The lesion involves the leg · self-categorized by the patient as a rash · the lesion is described as raised or bumpy · the photograph is a close-up of the affected area · female contributor, age 60–69 · the lesion is associated with bothersome appearance and enlargement · present for less than one week: 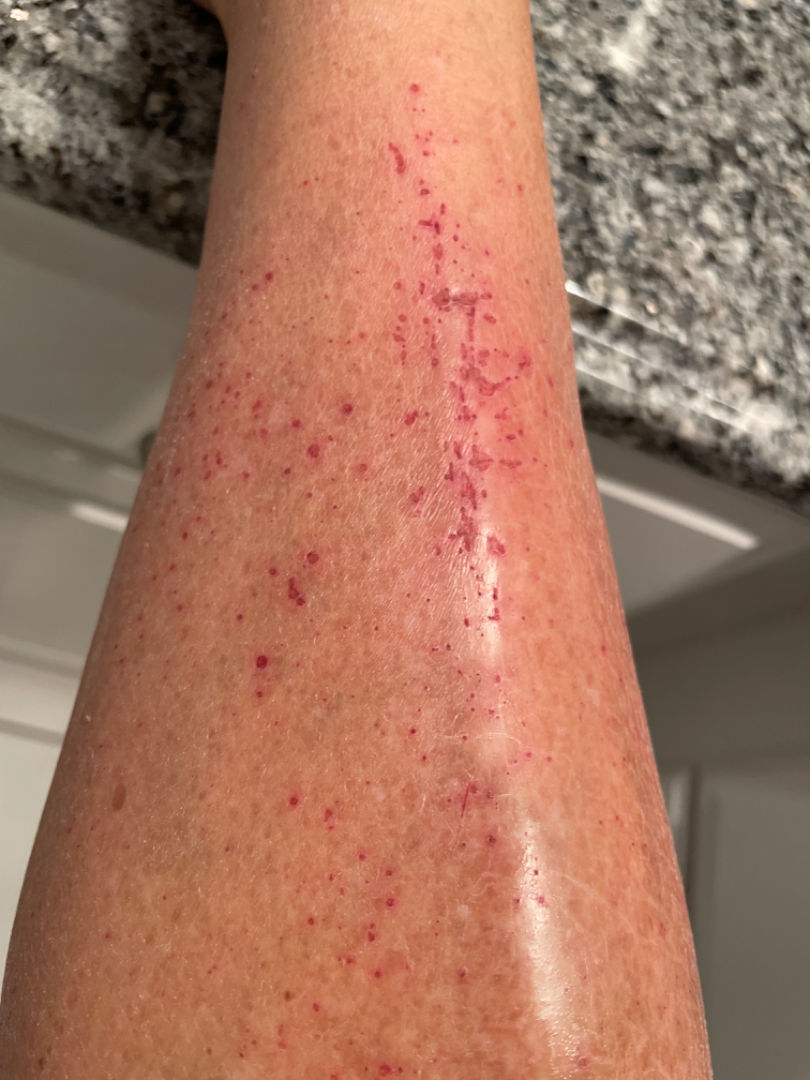differential diagnosis — most consistent with Eczema